A male patient aged 89; a clinical photograph of a skin lesion.
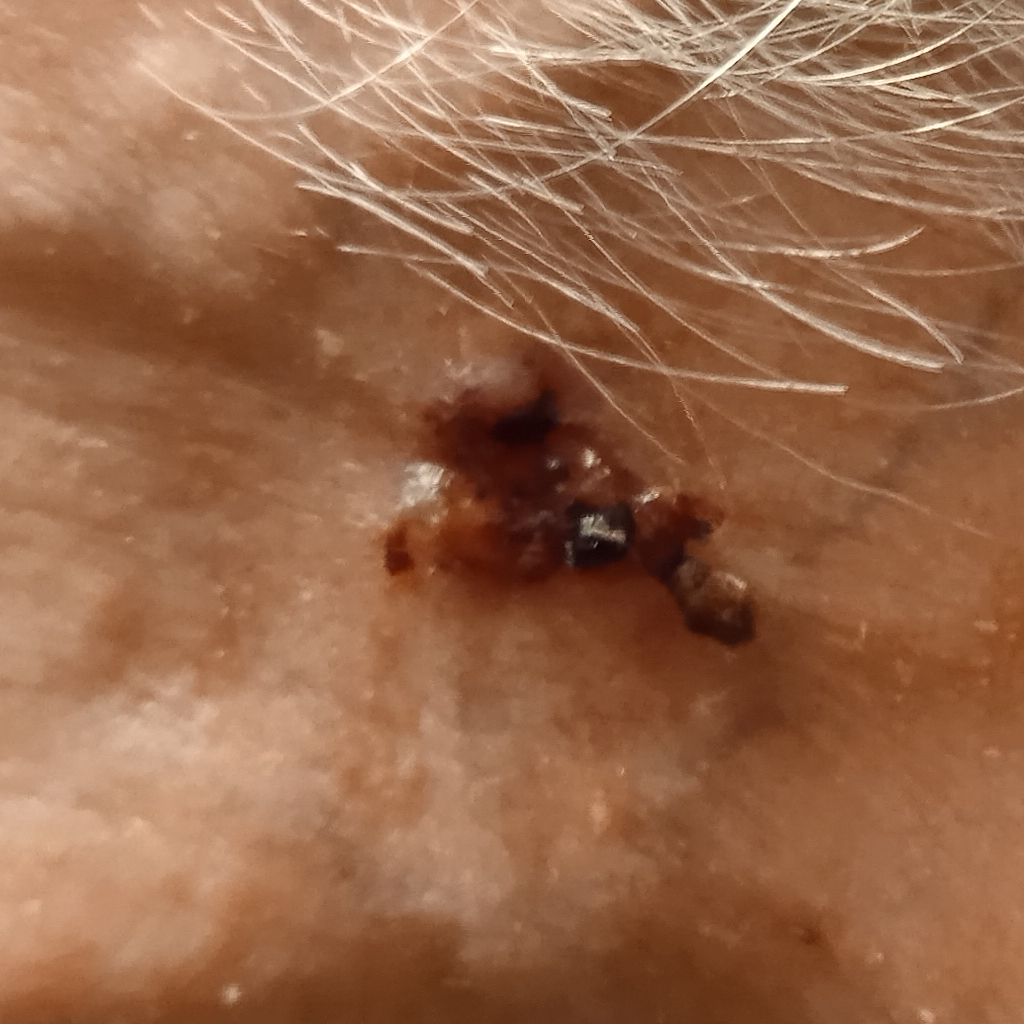Clinical context:
Located on the face. The lesion measures approximately 14.9 mm.
Conclusion:
On biopsy, the diagnosis was a basal cell carcinoma, following excision, with tumor thickness 2 mm.